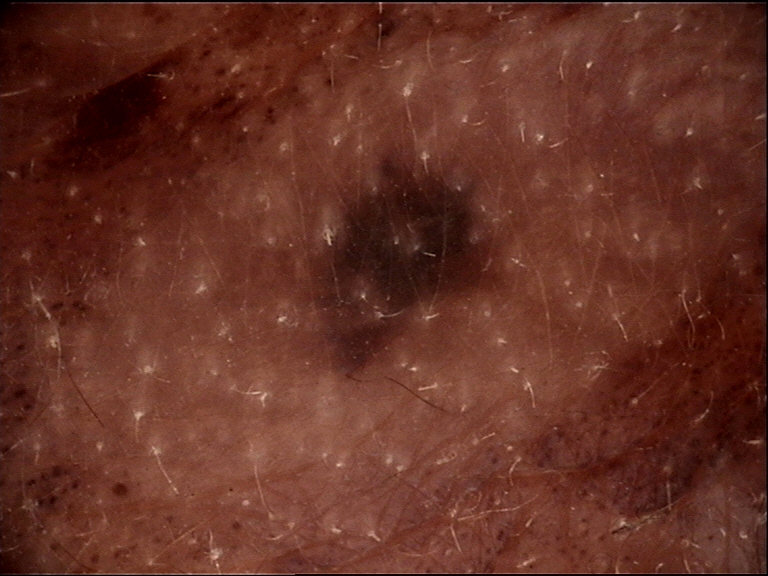Classified as a congenital compound nevus.